A skin lesion imaged with a dermatoscope: 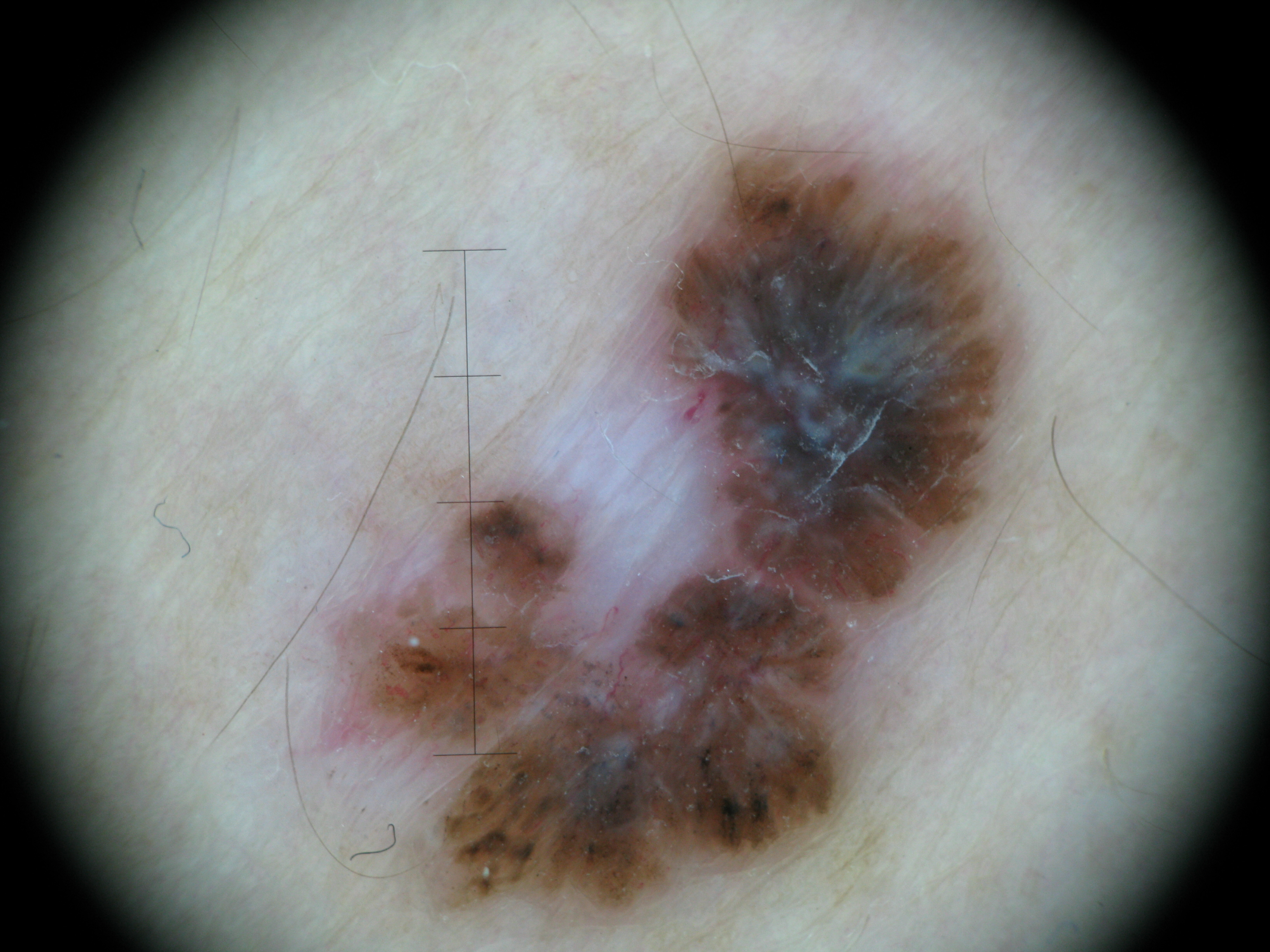lesion type: keratinocytic, diagnosis: basal cell carcinoma (biopsy-proven).